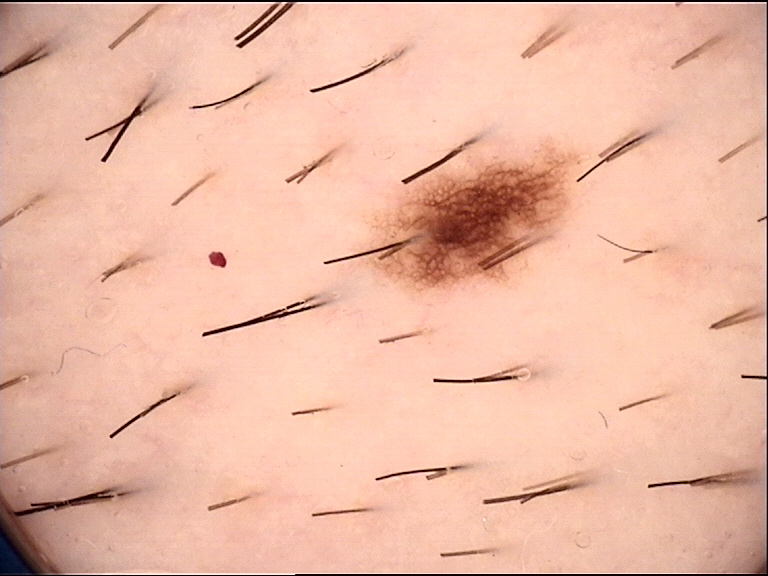imaging = dermatoscopy, class = dysplastic junctional nevus (expert consensus).